The photograph is a close-up of the affected area.
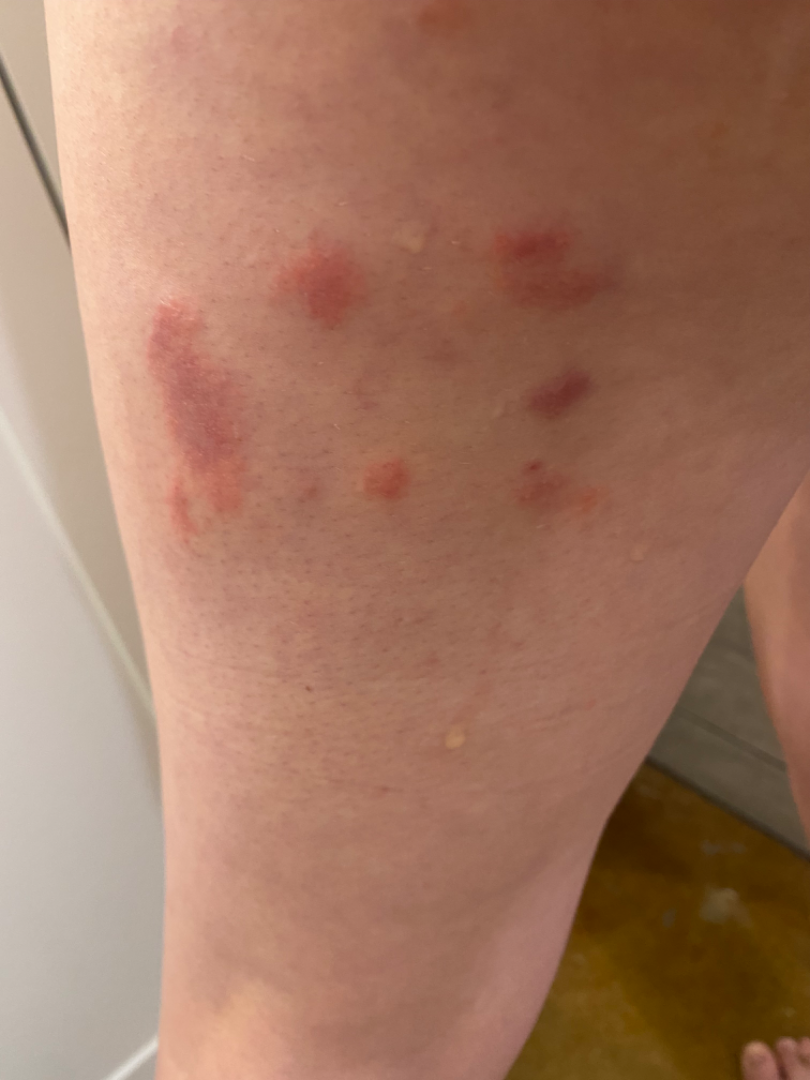– assessment: indeterminate